Recorded as Fitzpatrick II — 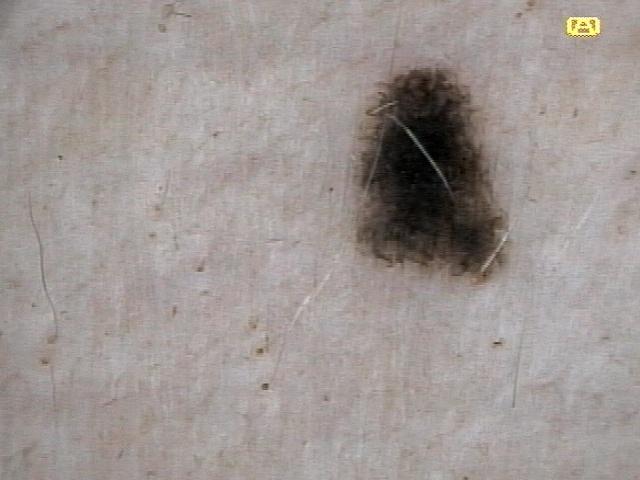- anatomic site — the trunk
- diagnostic label — Nevus (biopsy-proven)